Texture is reported as rough or flaky and raised or bumpy. The subject is a male aged 60–69. Close-up view. Located on the leg:
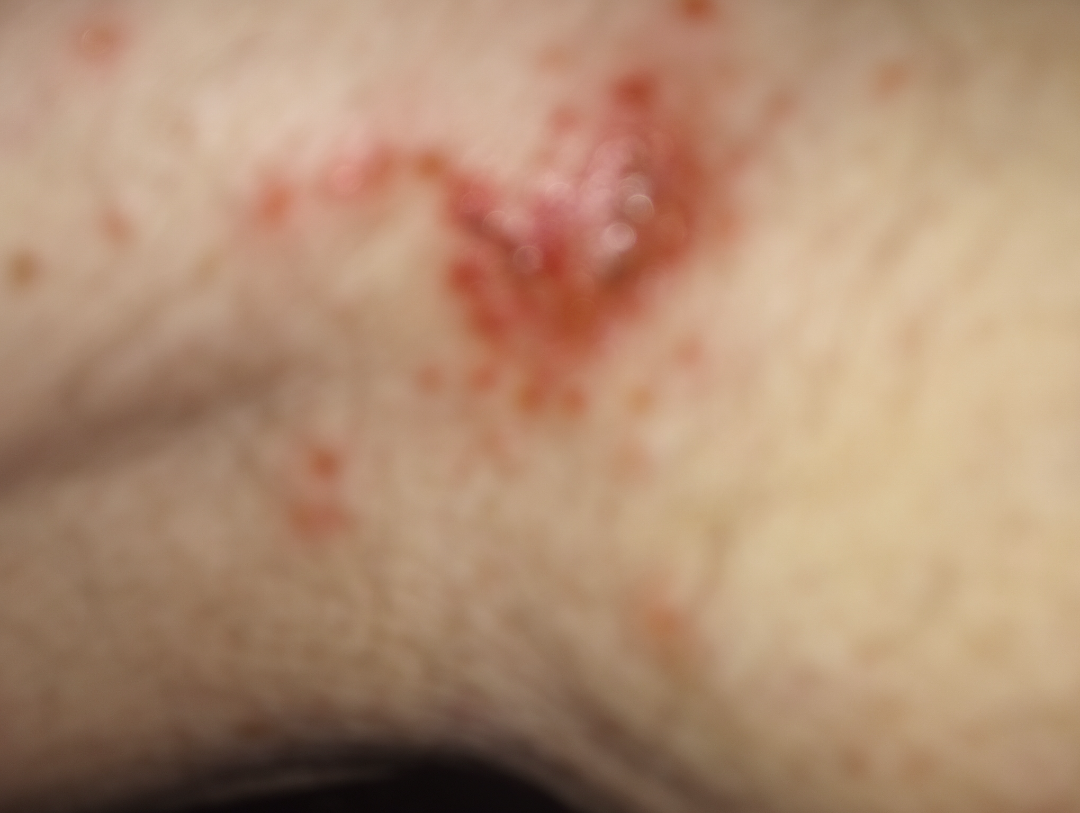  differential:
    tied_lead:
      - Impetigo
      - Herpes Zoster
    unlikely:
      - Infected eczema